A clinical photograph showing a skin lesion — 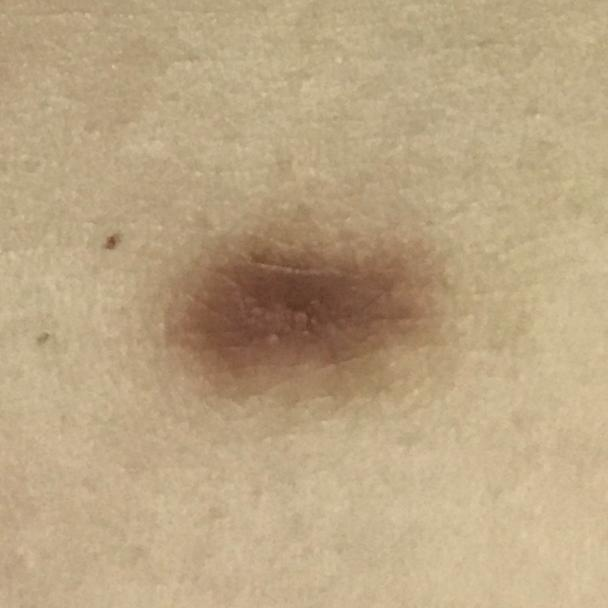<lesion>
  <lesion_location>the abdomen</lesion_location>
  <symptoms>
    <present>growth</present>
  </symptoms>
  <diagnosis>
    <name>nevus</name>
    <code>NEV</code>
    <malignancy>benign</malignancy>
    <confirmation>clinical consensus</confirmation>
  </diagnosis>
</lesion>